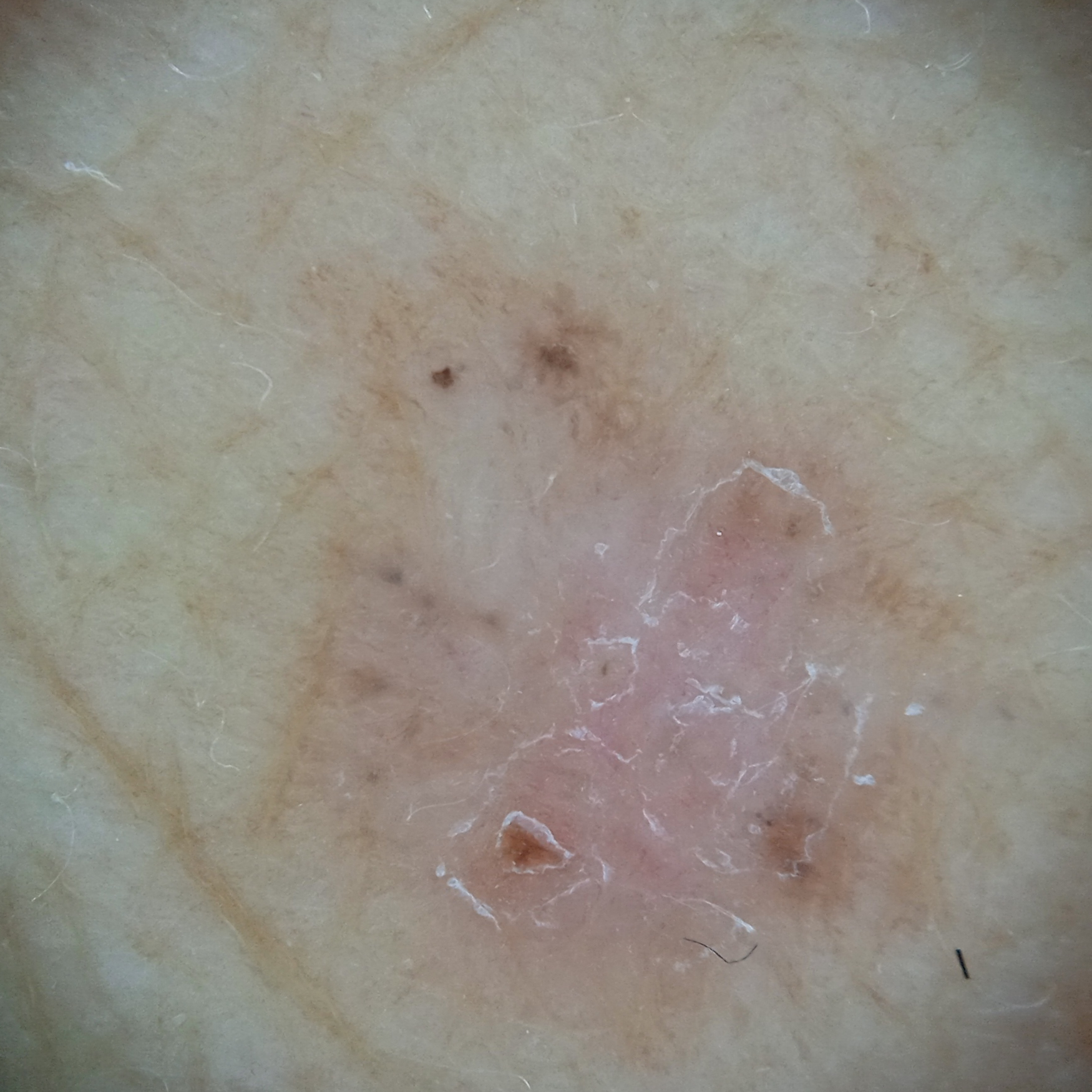The patient says their skin tans without first burning. The patient describes having a moderate number of moles. A skin lesion imaged with a dermatoscope. The patient reports a family history of skin cancer and a personal history of cancer. A female patient 64 years of age. Located on the torso. On biopsy, the diagnosis was a basal cell carcinoma, following a punch biopsy, with a measured tumor thickness of 0.6 mm.